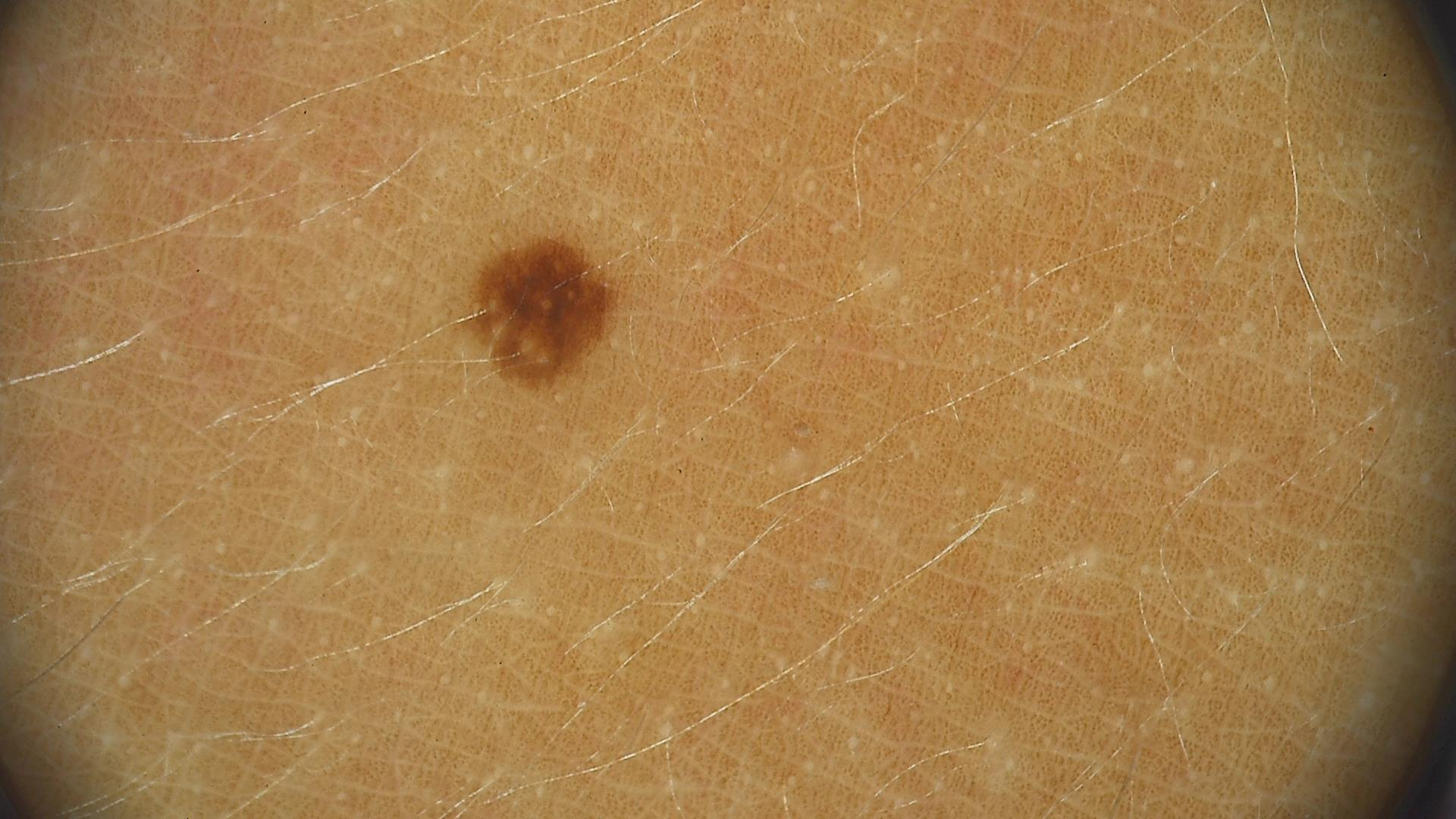assessment: junctional nevus (expert consensus).